A dermoscopic image of a skin lesion — 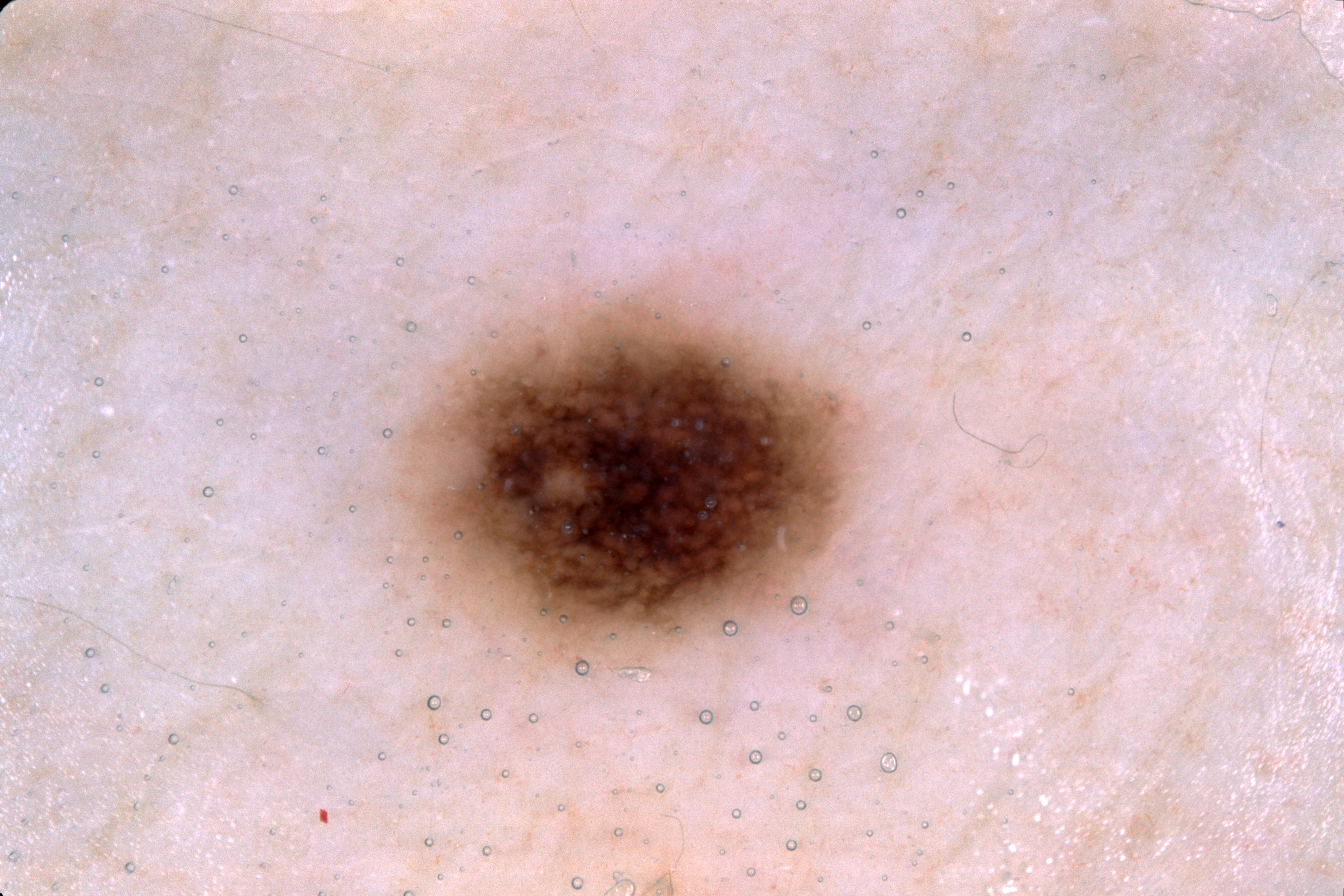<case>
  <lesion_location>
    <bbox_xyxy>375, 273, 878, 683</bbox_xyxy>
  </lesion_location>
  <dermoscopic_features>
    <present>pigment network</present>
    <absent>milia-like cysts, streaks, negative network</absent>
  </dermoscopic_features>
  <diagnosis>
    <name>melanocytic nevus</name>
    <malignancy>benign</malignancy>
    <lineage>melanocytic</lineage>
    <provenance>clinical</provenance>
  </diagnosis>
</case>